Fitzpatrick skin type III · a smartphone photograph of a skin lesion · a female subject 46 years old:
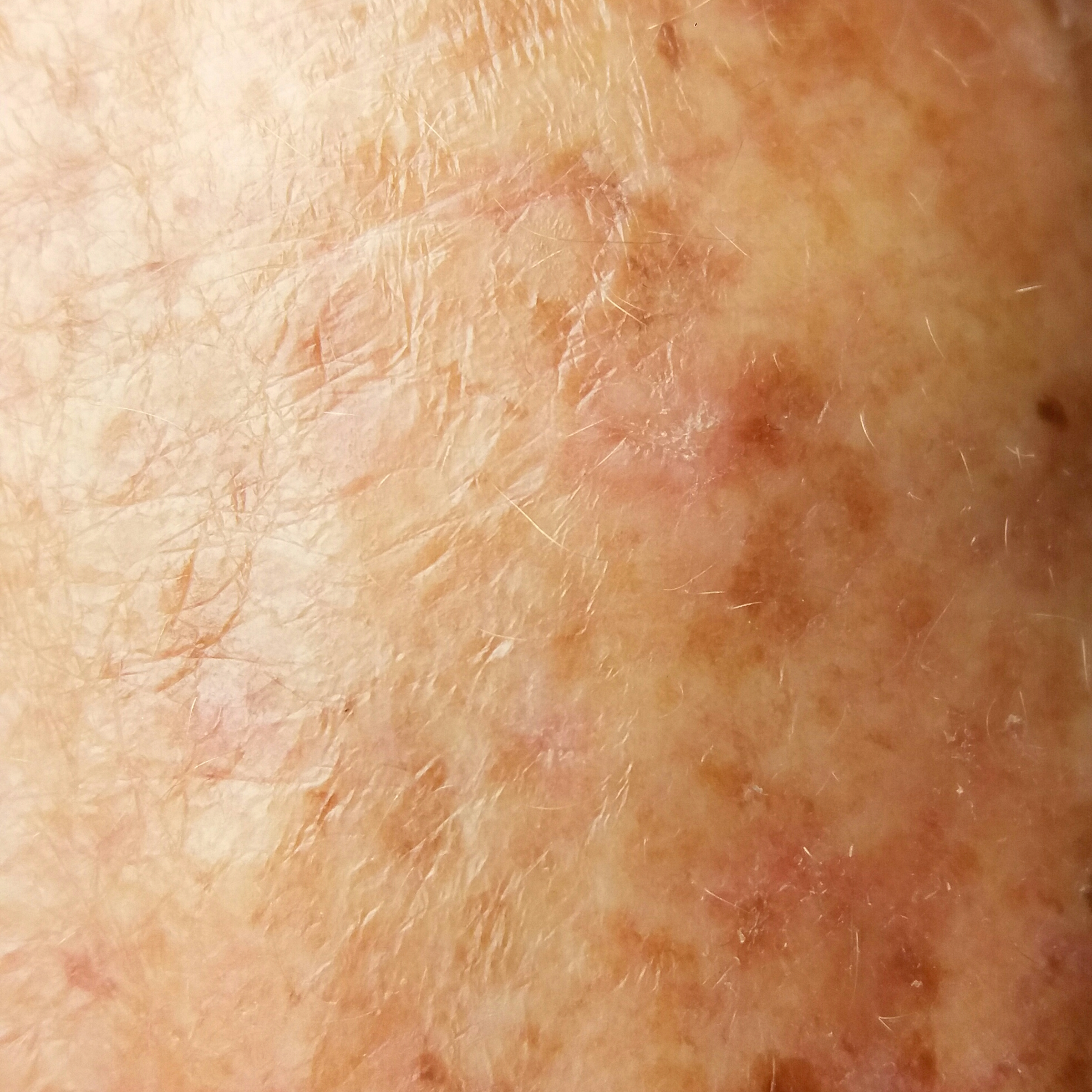By the patient's account, the lesion itches. The consensus clinical diagnosis was an actinic keratosis.